A dermoscopic close-up of a skin lesion.
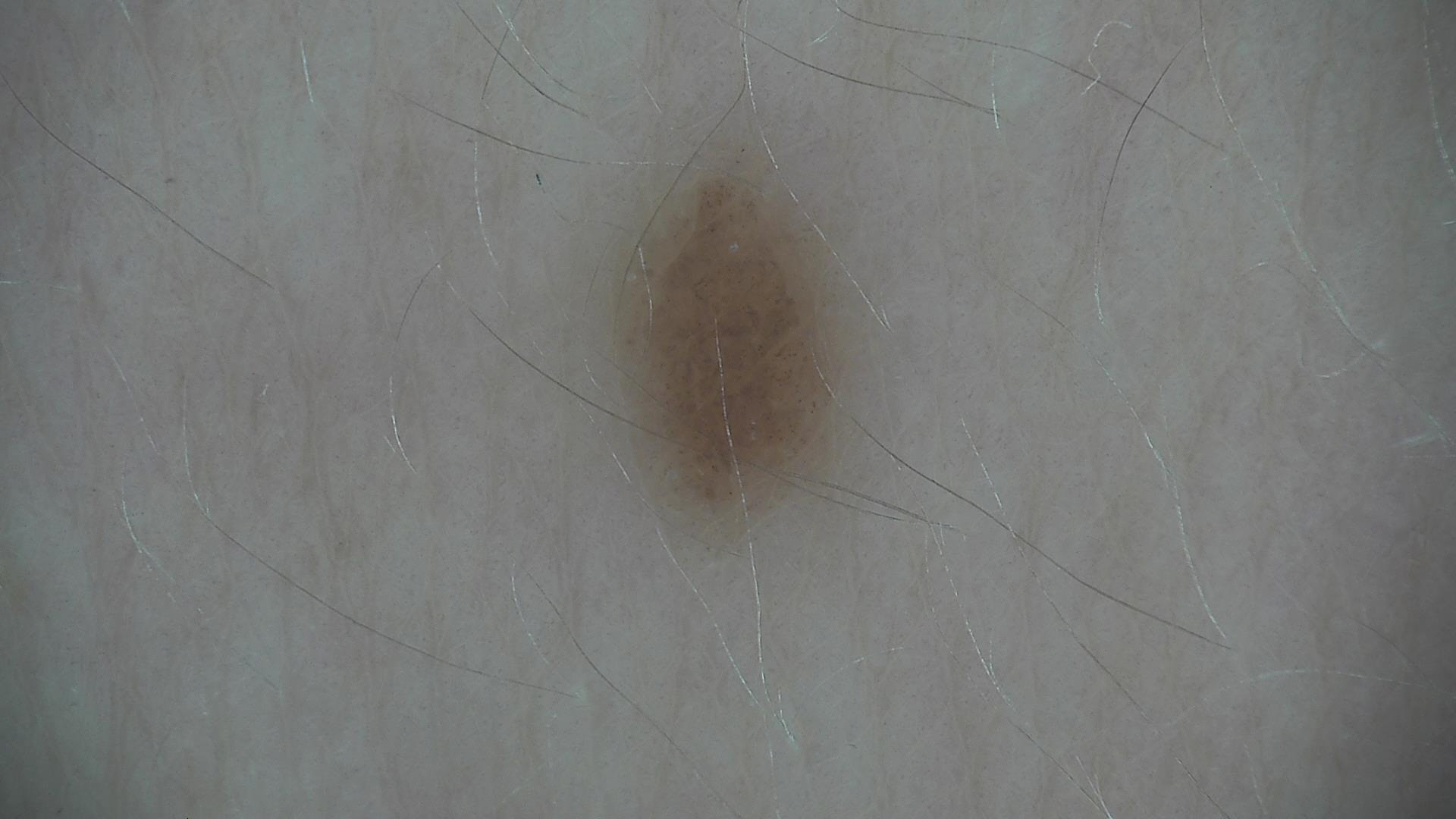Consistent with a dysplastic junctional nevus.